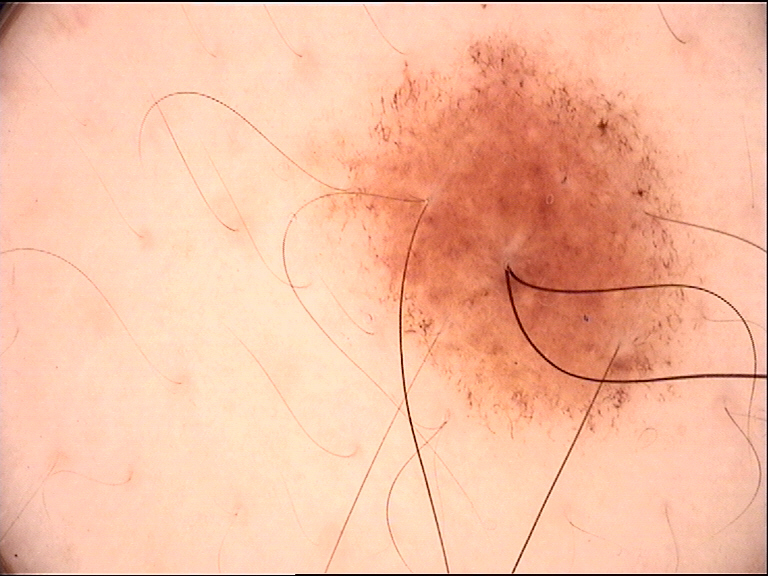Findings: A dermoscopic close-up of a skin lesion. Impression: Diagnosed as a benign lesion — a dysplastic compound nevus.